A dermoscopic photograph of a skin lesion: 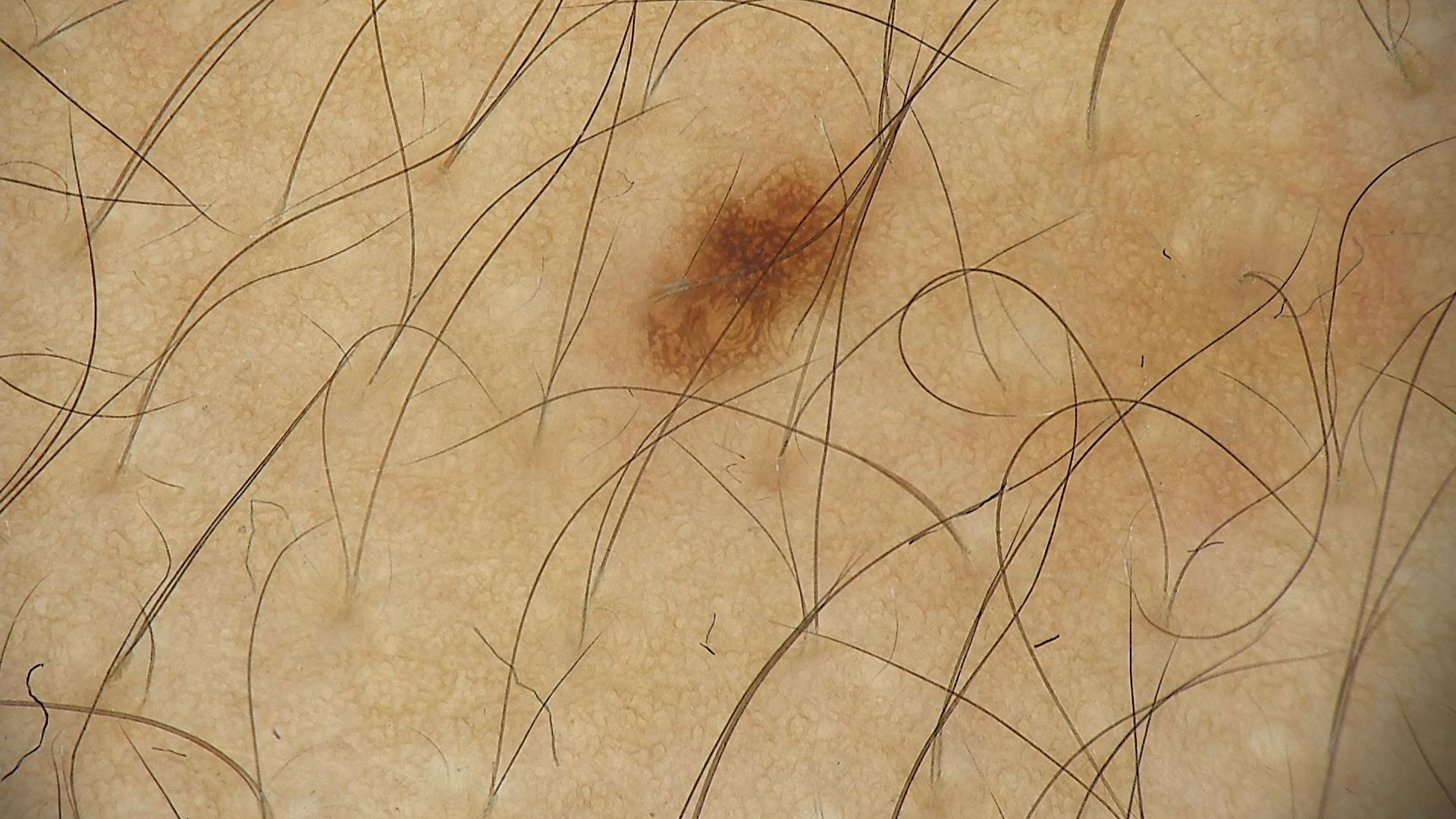label=dysplastic junctional nevus (expert consensus).